A dermoscopic image of a skin lesion.
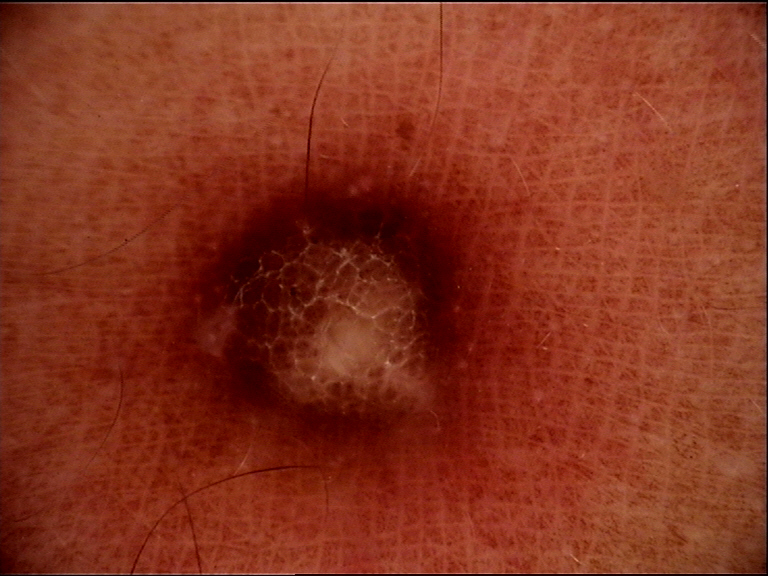Diagnosed as a dermatofibroma.